Dermoscopy of a skin lesion.
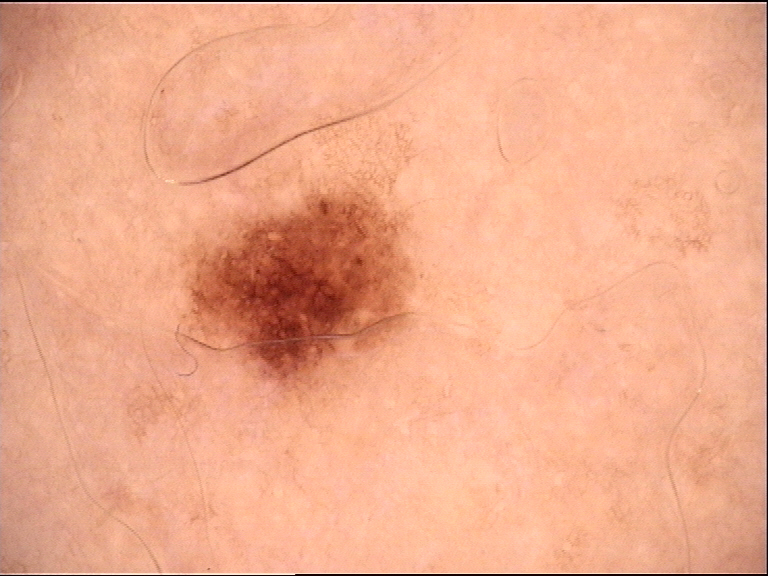The diagnosis was a benign lesion — a dysplastic junctional nevus.